A dermoscopic view of a skin lesion, a male subject in their 60s:
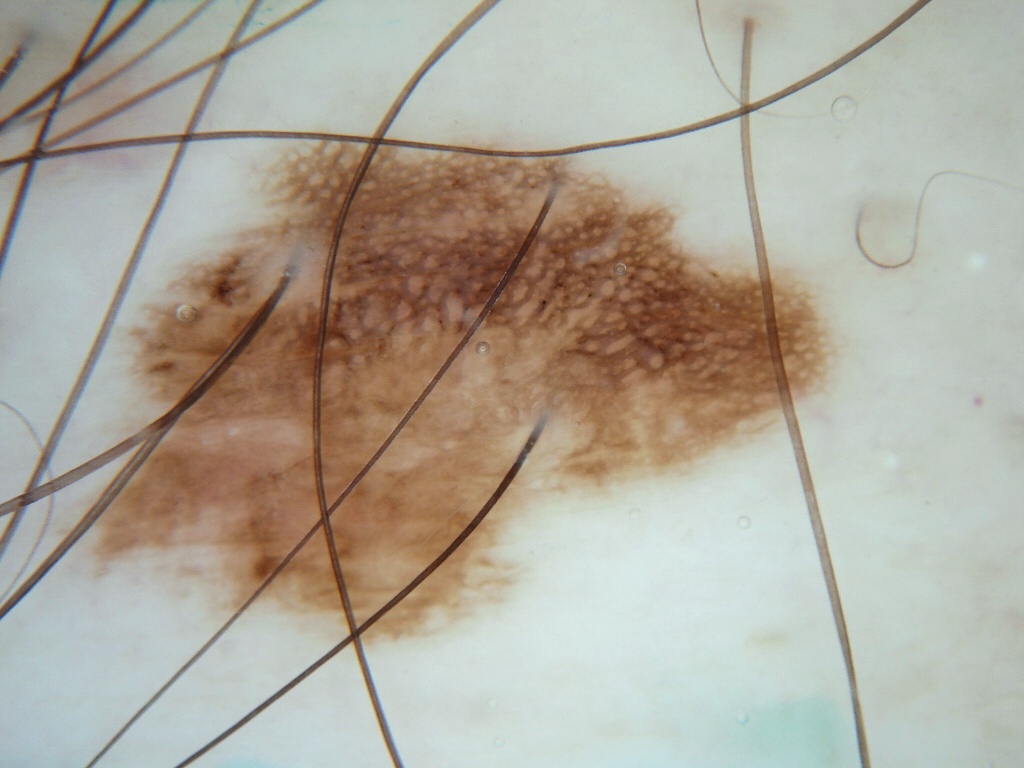{
  "lesion_extent": {
    "approx_field_fraction_pct": 38
  },
  "lesion_location": {
    "bbox_xyxy": [
      52,
      115,
      837,
      660
    ]
  },
  "dermoscopic_features": {
    "present": [
      "pigment network"
    ],
    "absent": [
      "negative network",
      "streaks",
      "globules",
      "milia-like cysts"
    ]
  },
  "diagnosis": {
    "name": "melanocytic nevus",
    "malignancy": "benign",
    "lineage": "melanocytic",
    "provenance": "clinical"
  }
}